A dermoscopy image of a single skin lesion.
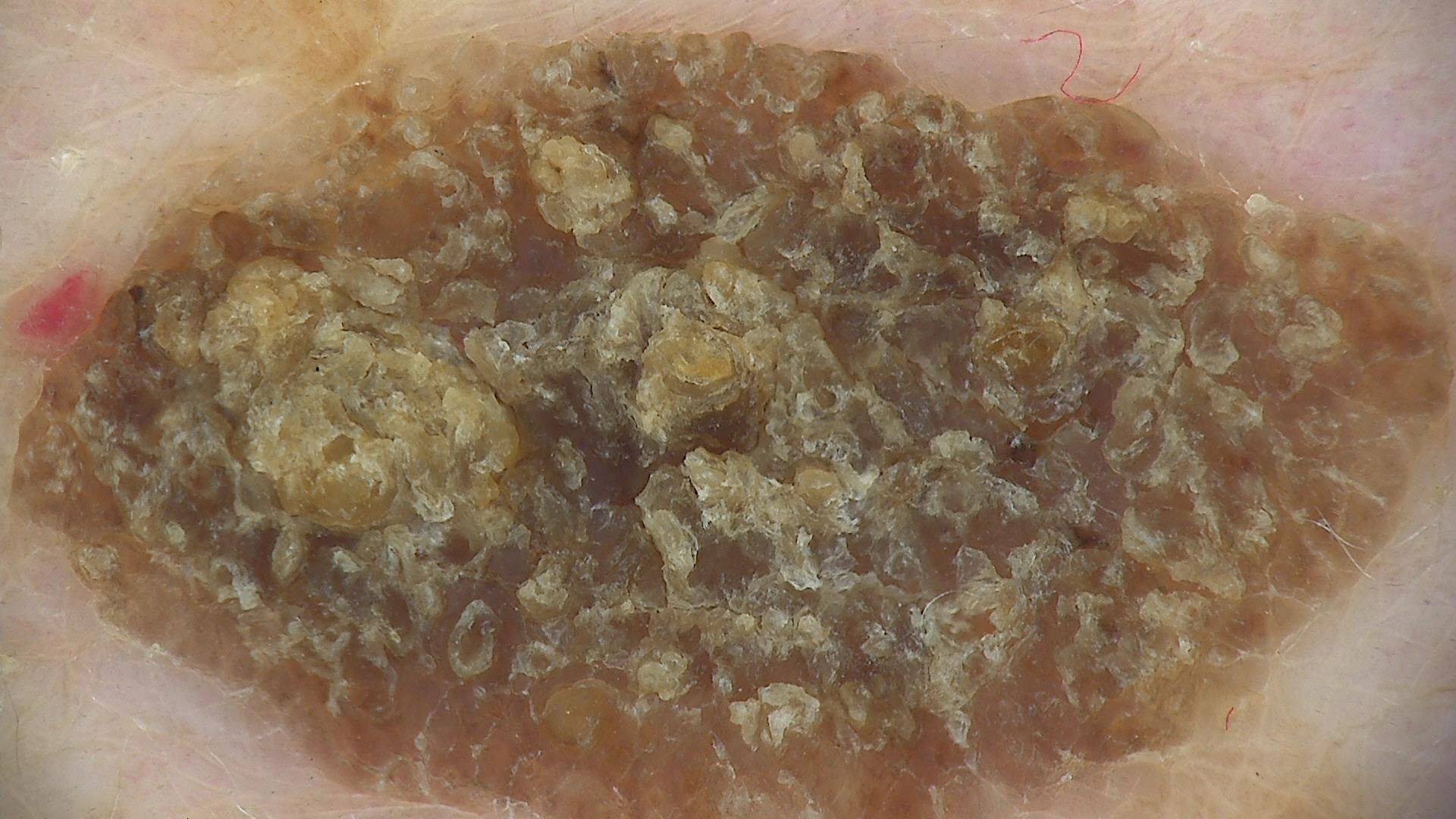The morphology is that of a keratinocytic lesion. The diagnosis was a seborrheic keratosis.